This image was taken at a distance.
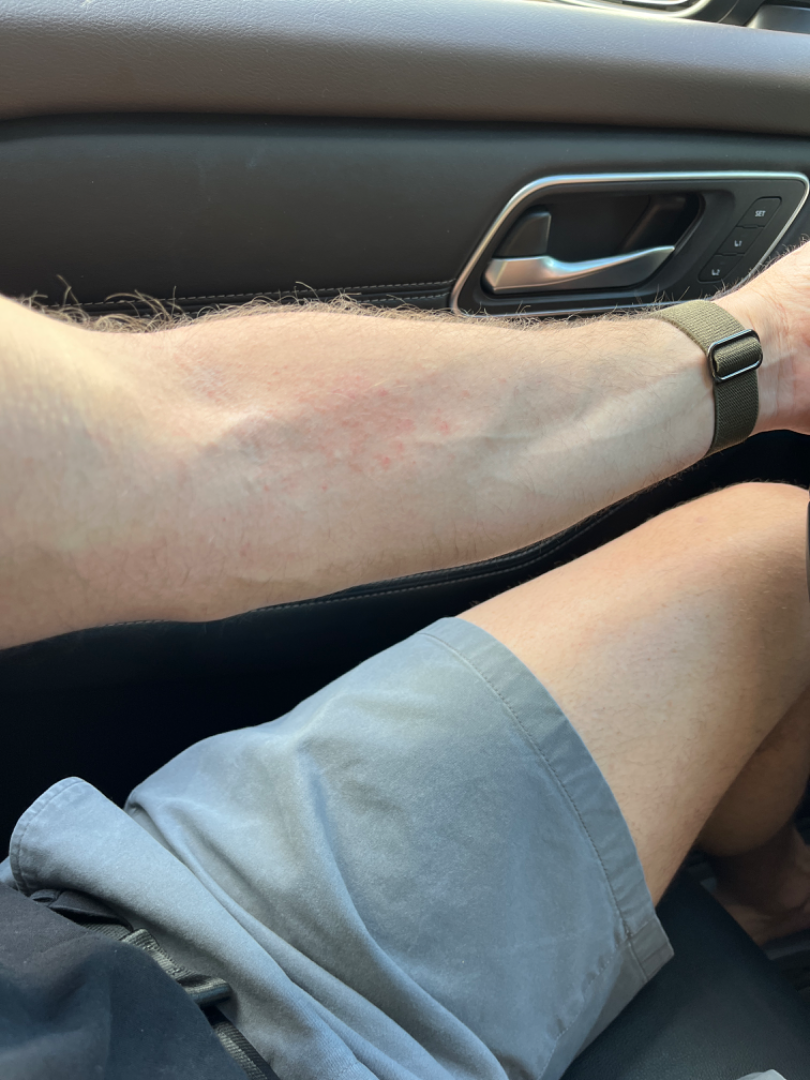Review: One reviewing dermatologist: the favored diagnosis is Eczema; the differential also includes Drug Rash; also raised was Allergic Contact Dermatitis.